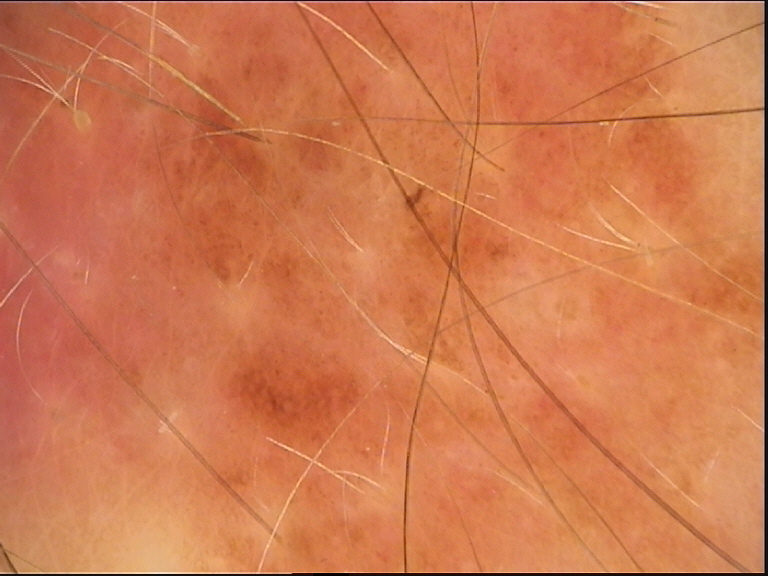diagnostic label = dysplastic junctional nevus (expert consensus).